Present for less than one week; reported lesion symptoms include burning and bothersome appearance; the photograph was taken at a distance; the lesion involves the leg; the lesion is described as rough or flaky; self-categorized by the patient as a rash; the contributor is 18–29, male:
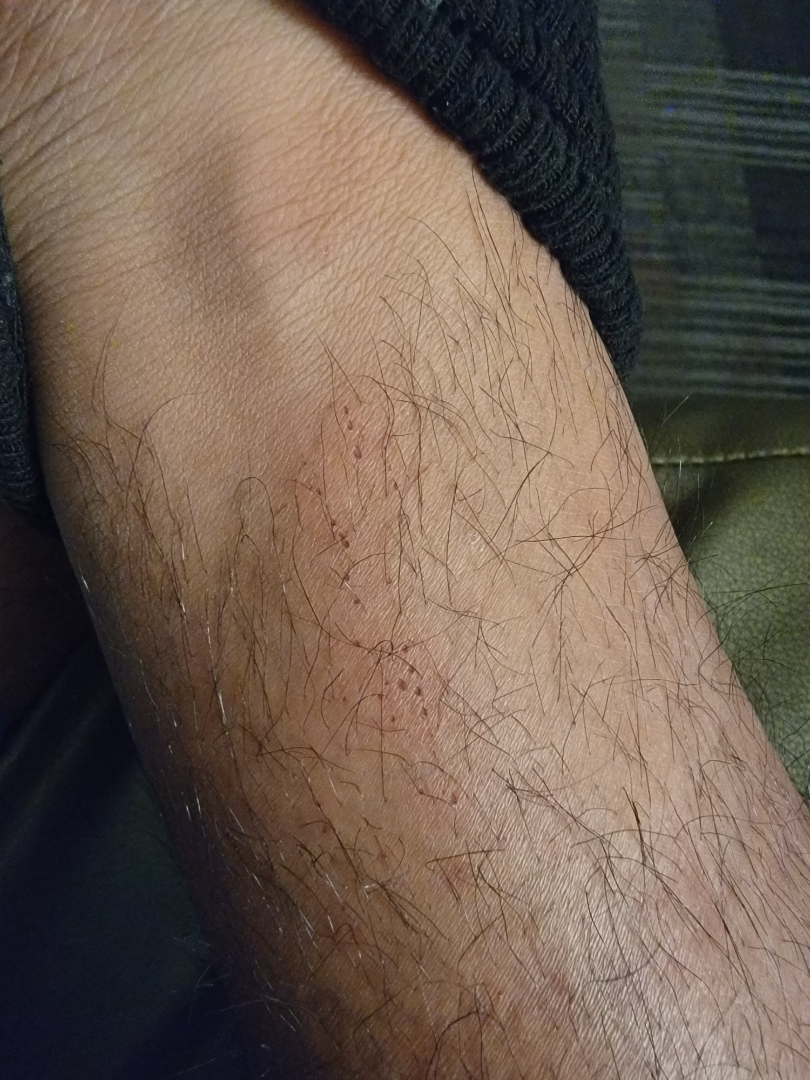The skin condition could not be confidently assessed from this image.